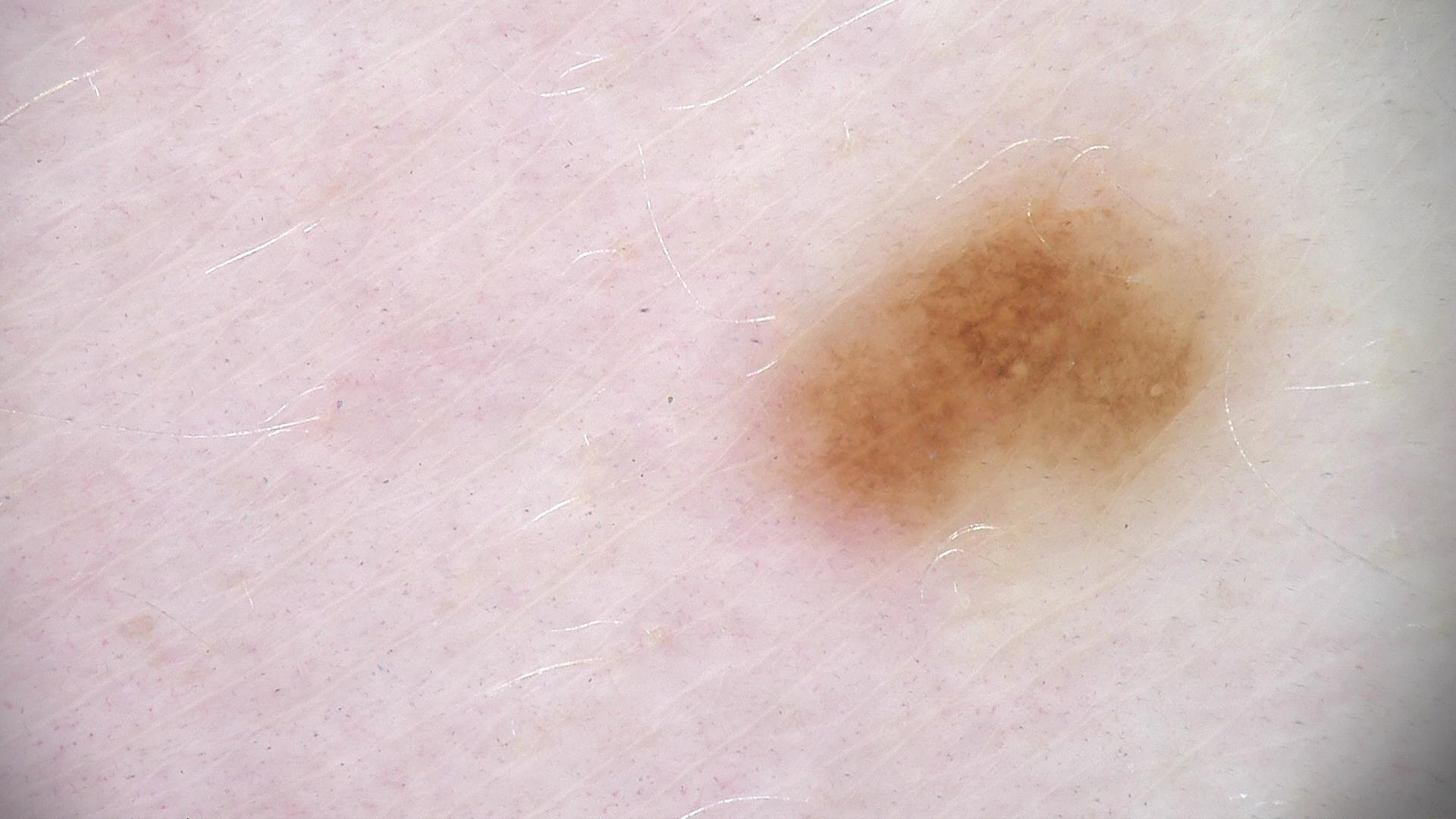Impression: Consistent with a dysplastic junctional nevus.